A subject age 63 · a clinical close-up photograph of a skin lesion: 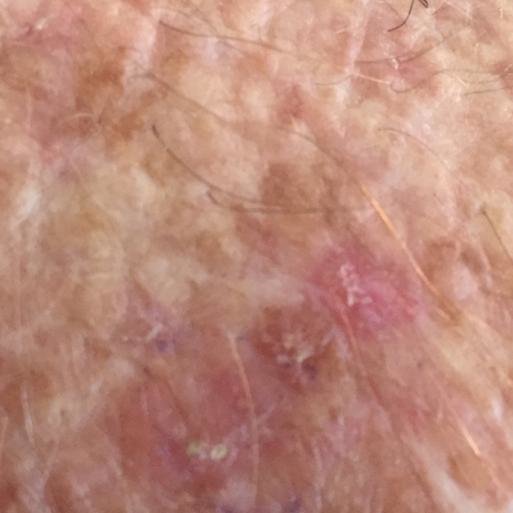By the patient's account, the lesion itches.
Clinically diagnosed as an actinic keratosis.